The lesion involves the leg, front of the torso, back of the torso and arm · the subject is a male aged 18–29 · a close-up photograph — 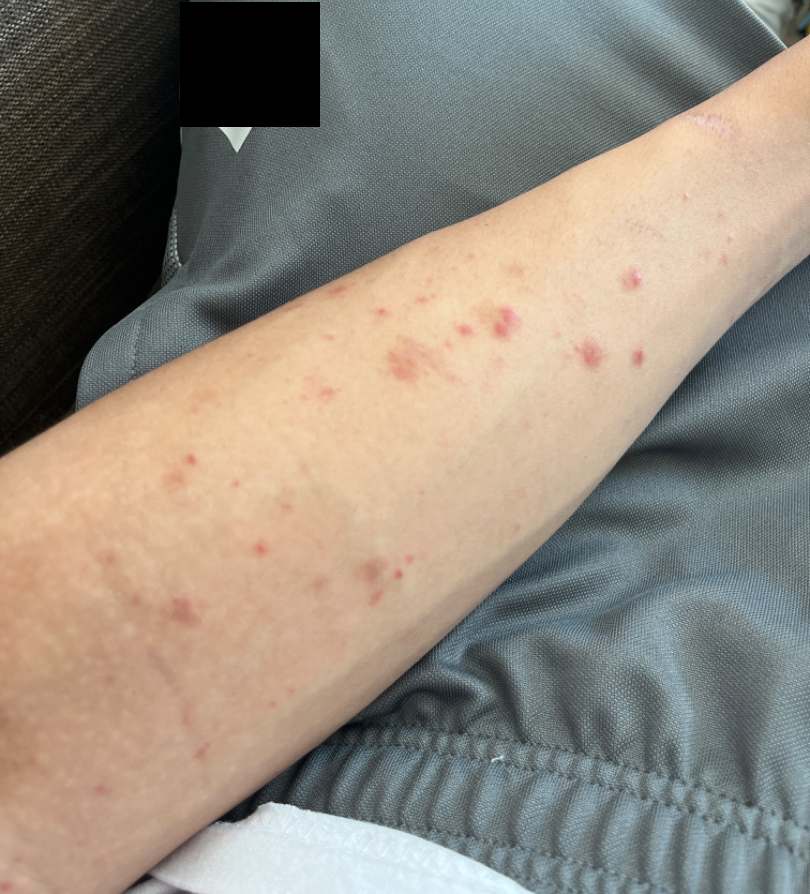reported symptoms: bothersome appearance and itching, patient's own categorization: acne, present for: one to three months, described texture: raised or bumpy, impression: the leading consideration is Insect Bite.